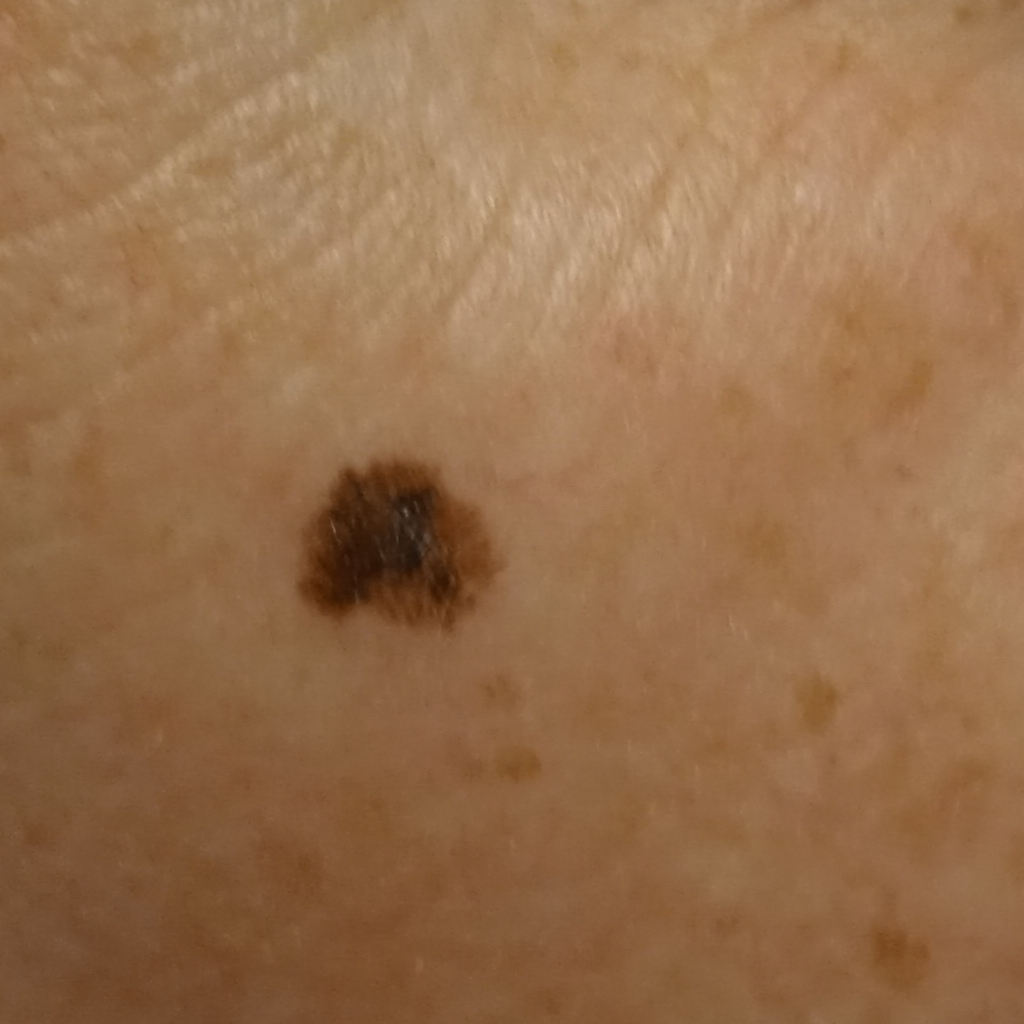A macroscopic clinical photograph of a skin lesion. By self-report, a personal history of skin cancer. A female subject 50 years of age. The patient describes having a moderate number of moles. Referred with a clinical suspicion of melanoma. The lesion involves the face. The biopsy diagnosis was a melanoma, following excision, with Breslow thickness 0.4 mm.